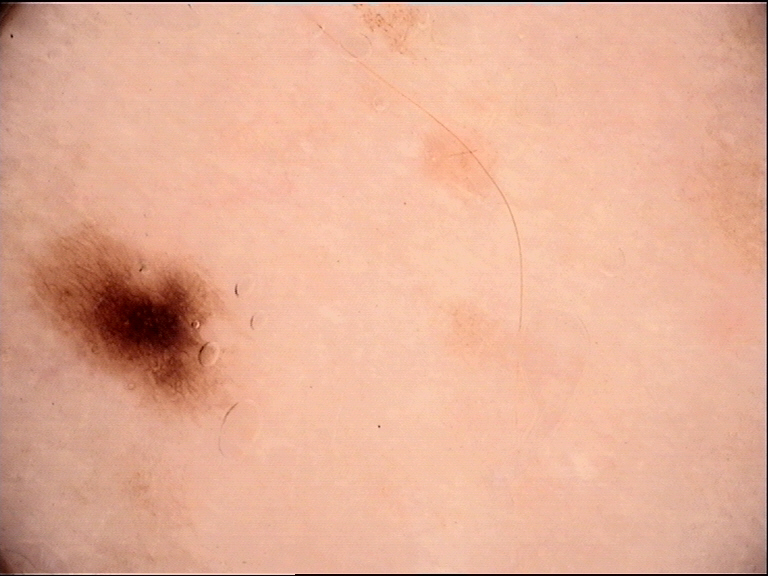Q: What is this lesion?
A: junctional nevus (expert consensus)